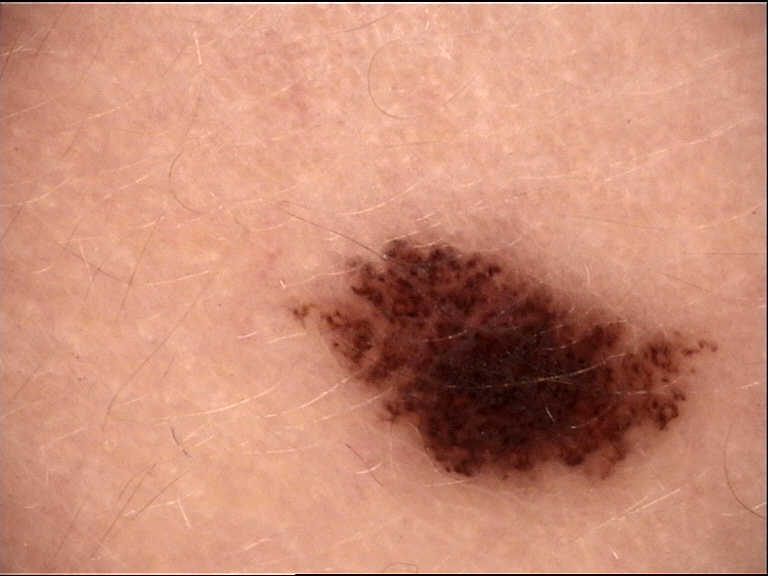Dermoscopy of a skin lesion. Consistent with a dysplastic compound nevus.